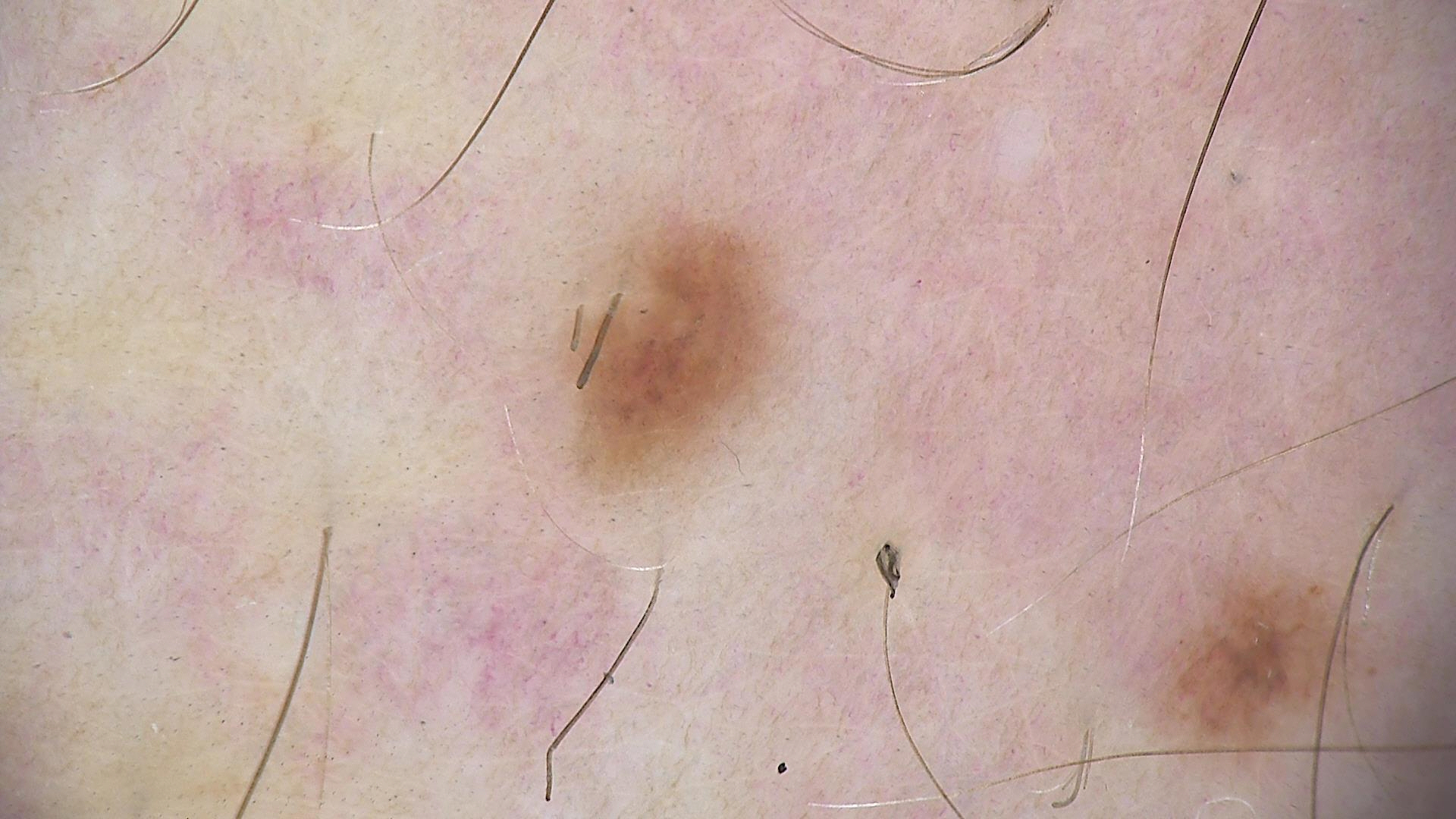Case:
- label · dysplastic junctional nevus (expert consensus)